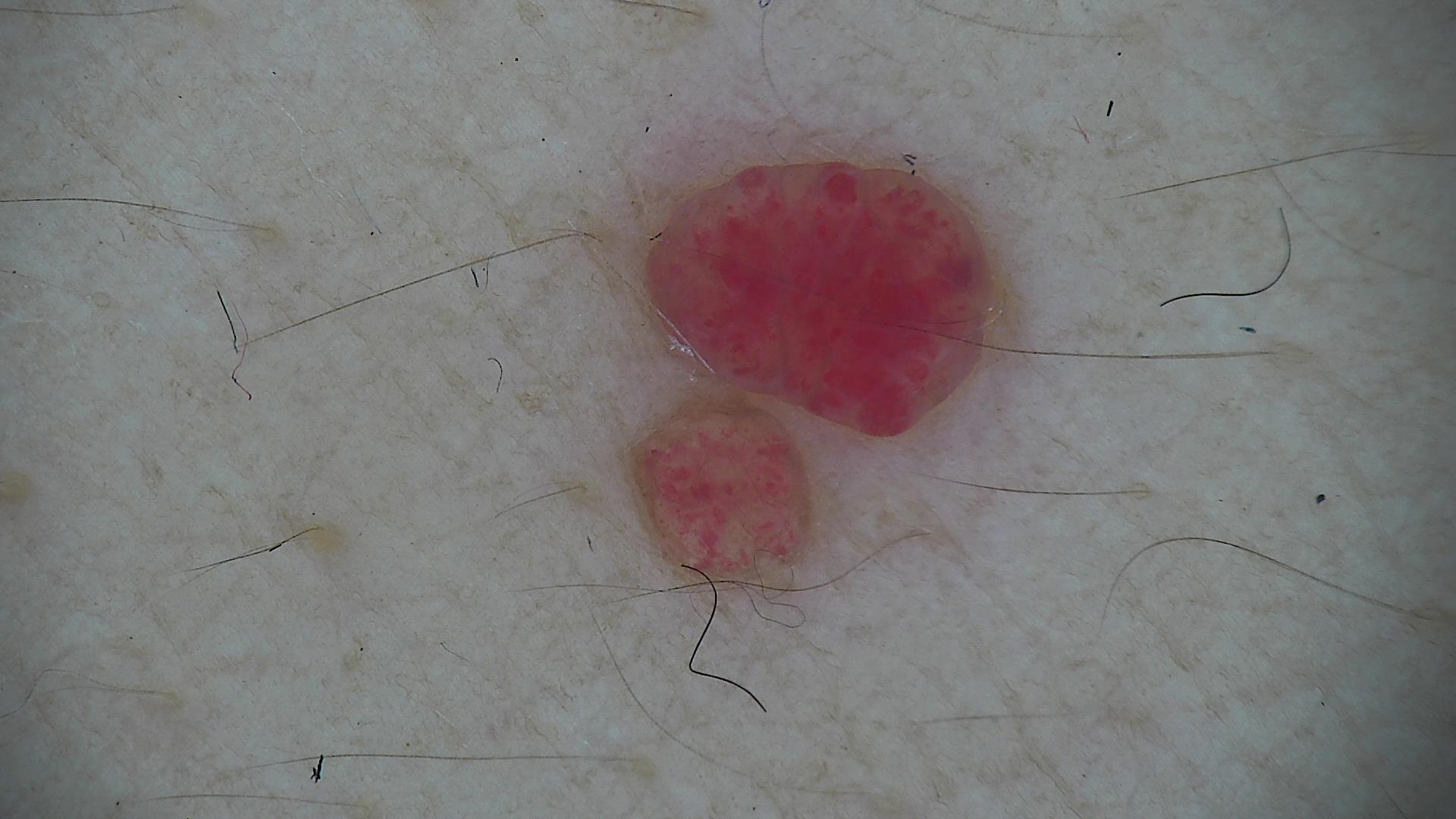A dermoscopic photograph of a skin lesion.
This is a vascular lesion.
The diagnostic label was a hemangioma.